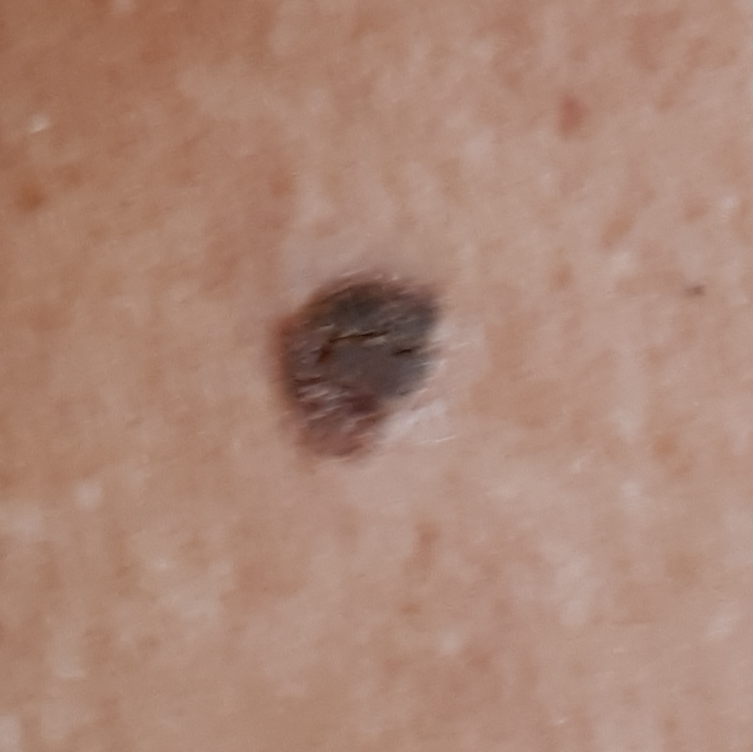A subject 88 years old.
Per patient report, the lesion is elevated and has grown.
Consistent with a seborrheic keratosis.